A clinical photograph showing a skin lesion. Collected as part of a research study, without a referral diagnosis. A female patient age 26:
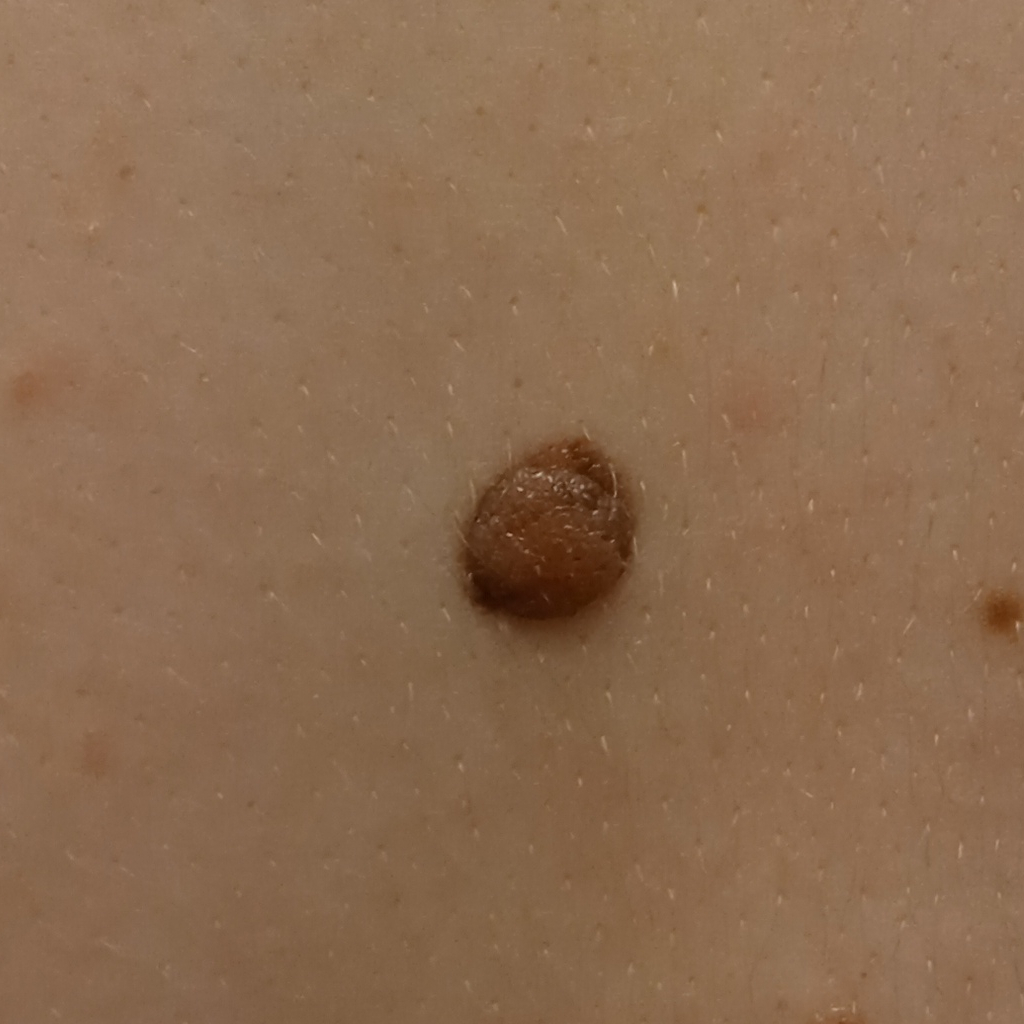• site: the back
• diameter: 8.9 mm
• assessment: melanocytic nevus (dermatologist consensus)